The chart records a prior melanoma · a female subject aged around 35 · a dermoscopy image of a single skin lesion · the patient is skin type II.
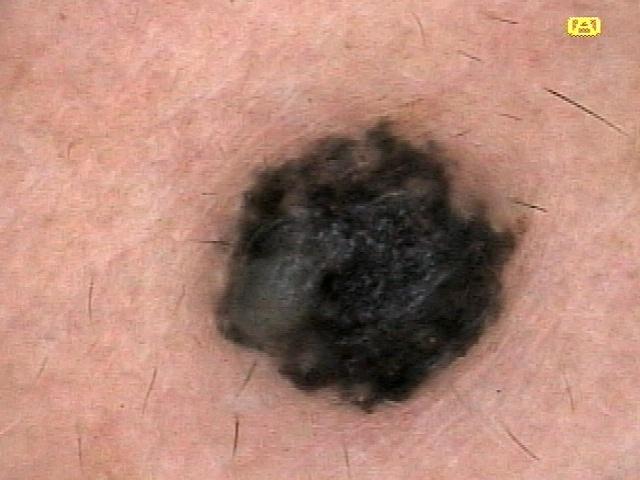Case summary:
Located on the head or neck.
Conclusion:
Histopathologically confirmed as a nevus.